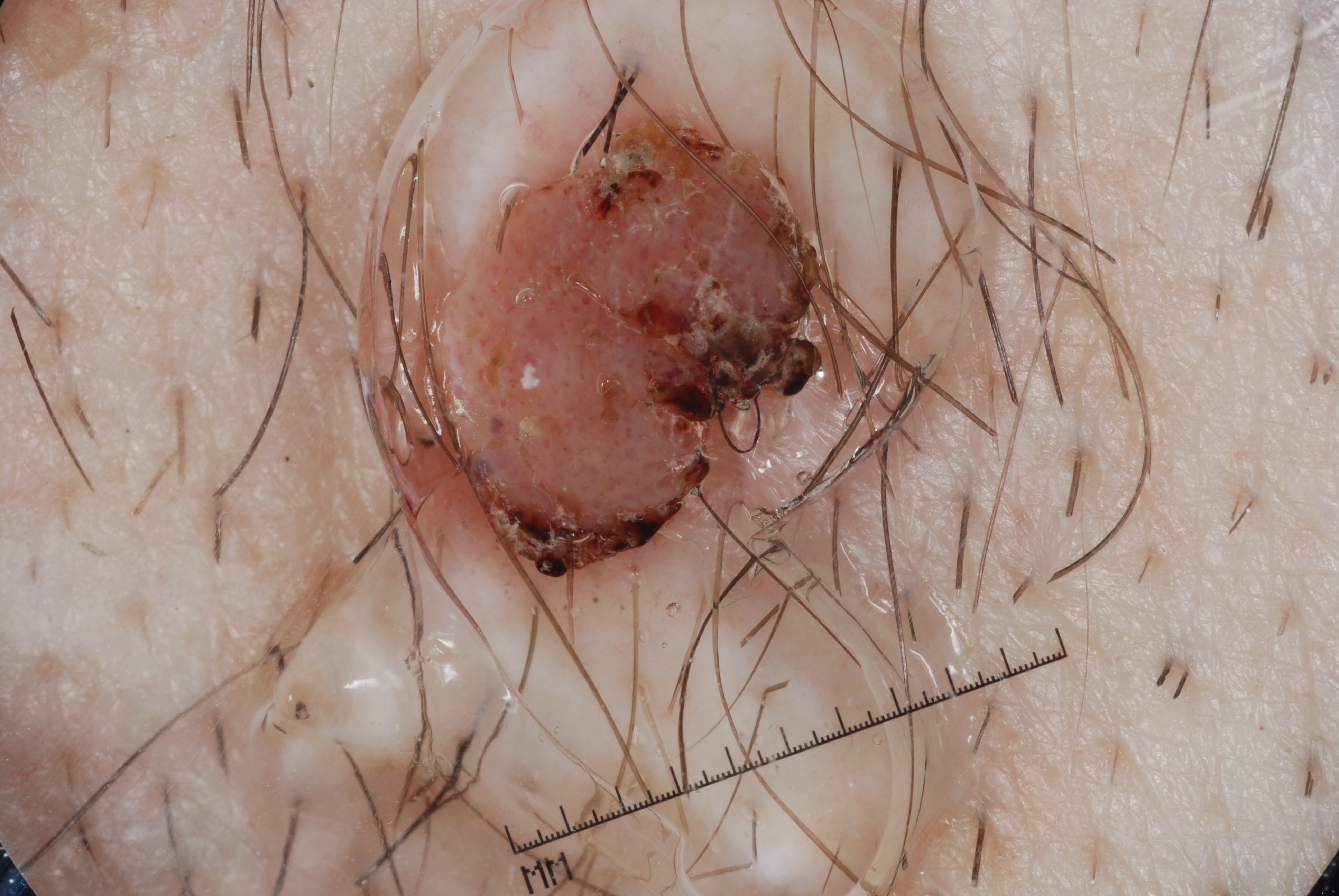Image and clinical context: Dermoscopy of a skin lesion. As (left, top, right, bottom), lesion location: 262, 77, 993, 630. Dermoscopically, the lesion shows no negative network, milia-like cysts, pigment network, or streaks. Conclusion: The lesion was assessed as a seborrheic keratosis.